A dermatoscopic image of a skin lesion: 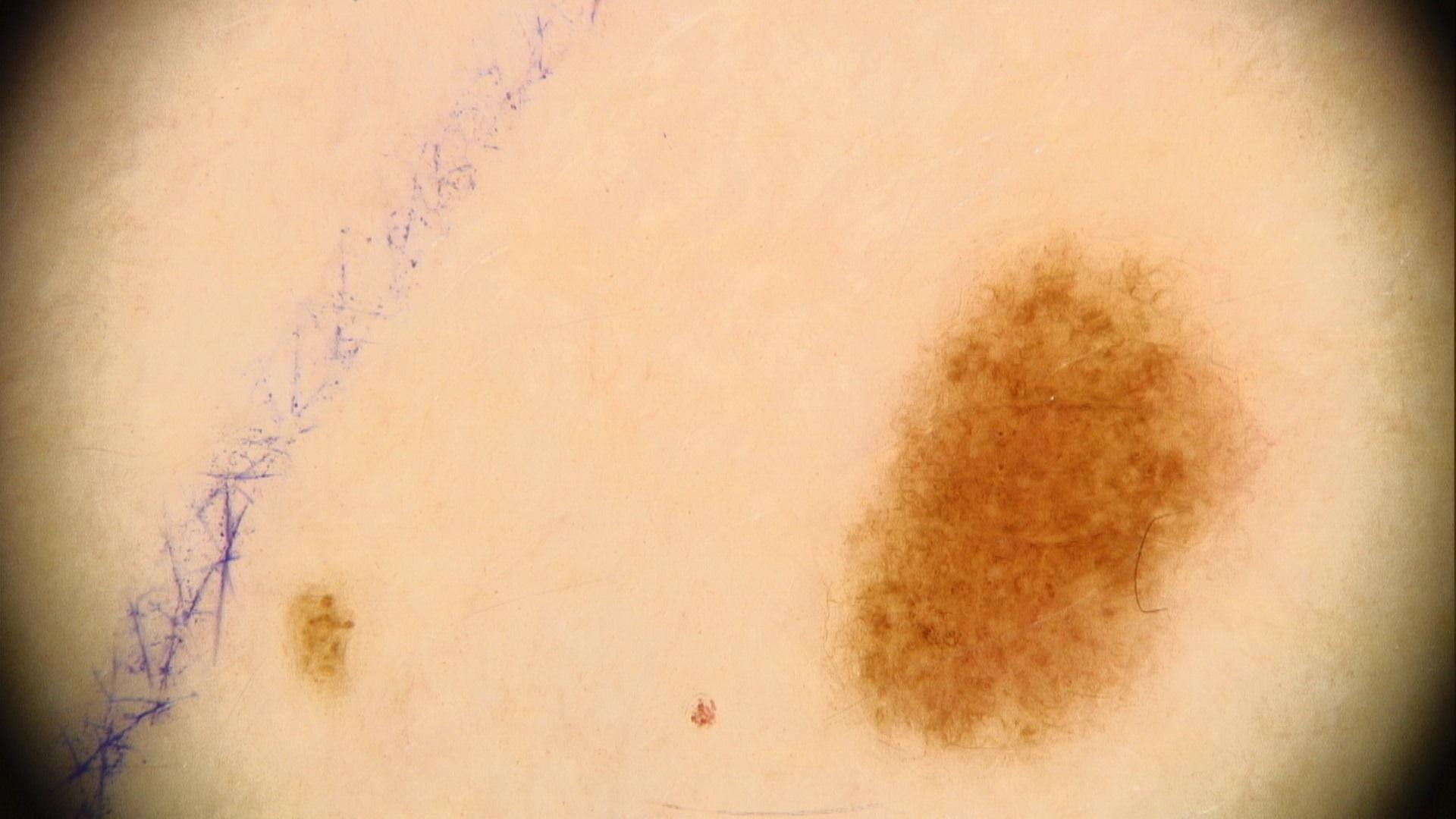anatomic site: the trunk
impression: Nevus